The photograph is a close-up of the affected area, located on the back of the hand, self-categorized by the patient as a growth or mole, reported lesion symptoms include bothersome appearance and enlargement, reported duration is one to three months.
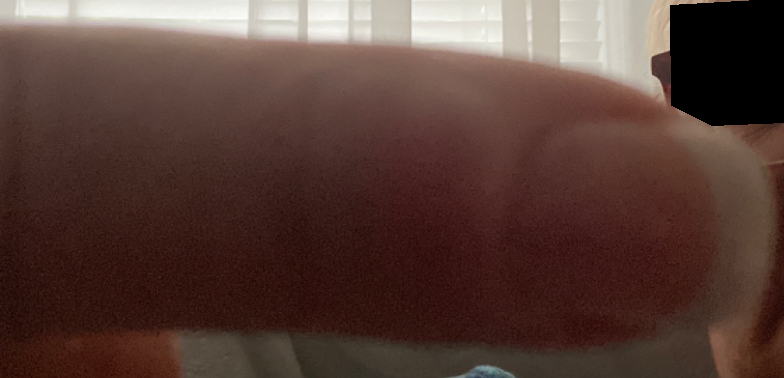Diagnostic features were not clearly distinguishable in this photograph.